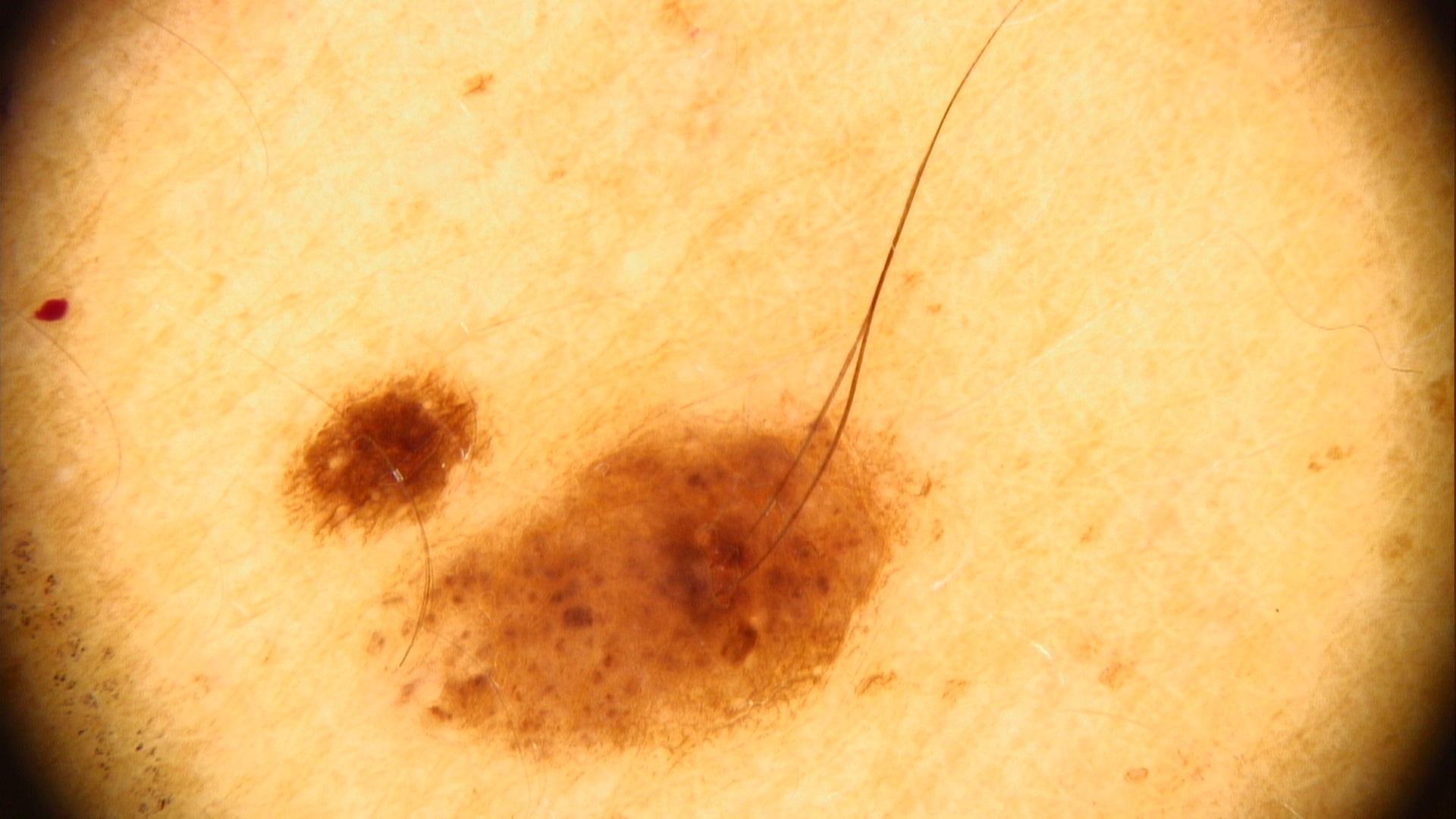Case summary:
A female subject in their mid-30s. Fitzpatrick III. A dermatoscopic image of a skin lesion.
Impression:
Consistent with a lesion of melanocytic origin — a nevus.